A dermoscopic image of a skin lesion.
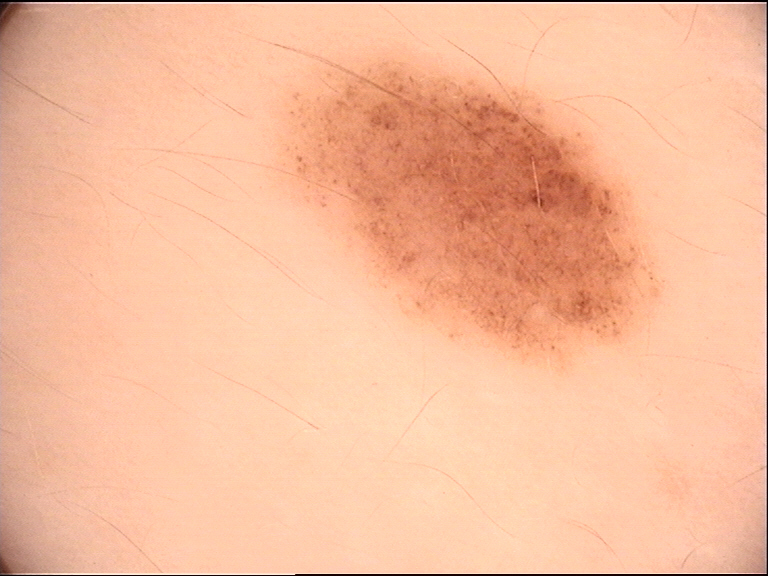Impression: The diagnostic label was a dysplastic junctional nevus.